A dermoscopic image of a skin lesion.
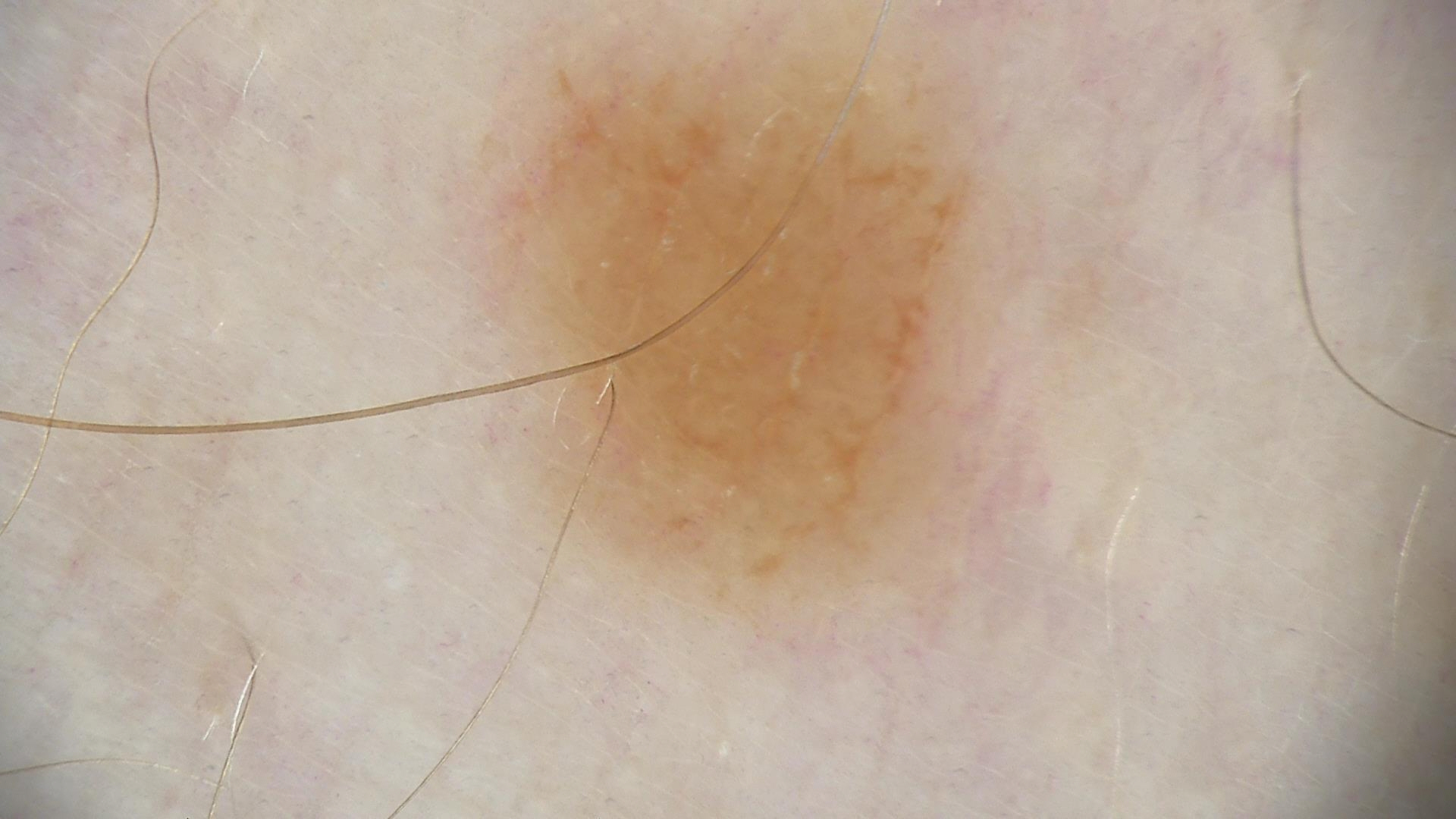{
  "diagnosis": {
    "name": "dysplastic junctional nevus",
    "code": "jd",
    "malignancy": "benign",
    "super_class": "melanocytic",
    "confirmation": "expert consensus"
  }
}